A dermoscopic close-up of a skin lesion: 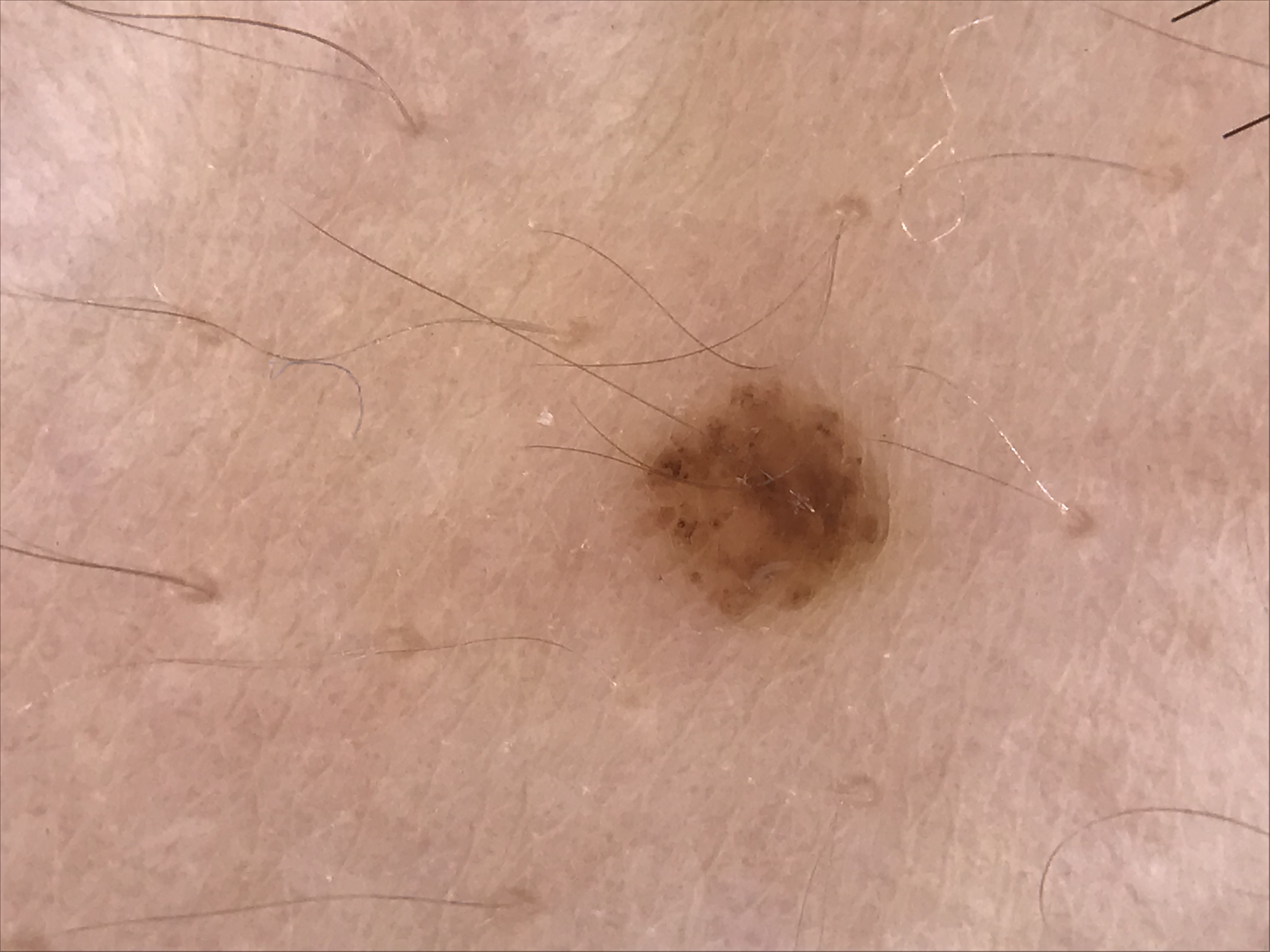This is a banal lesion.
The diagnostic label was a compound nevus.